The photograph is a close-up of the affected area: 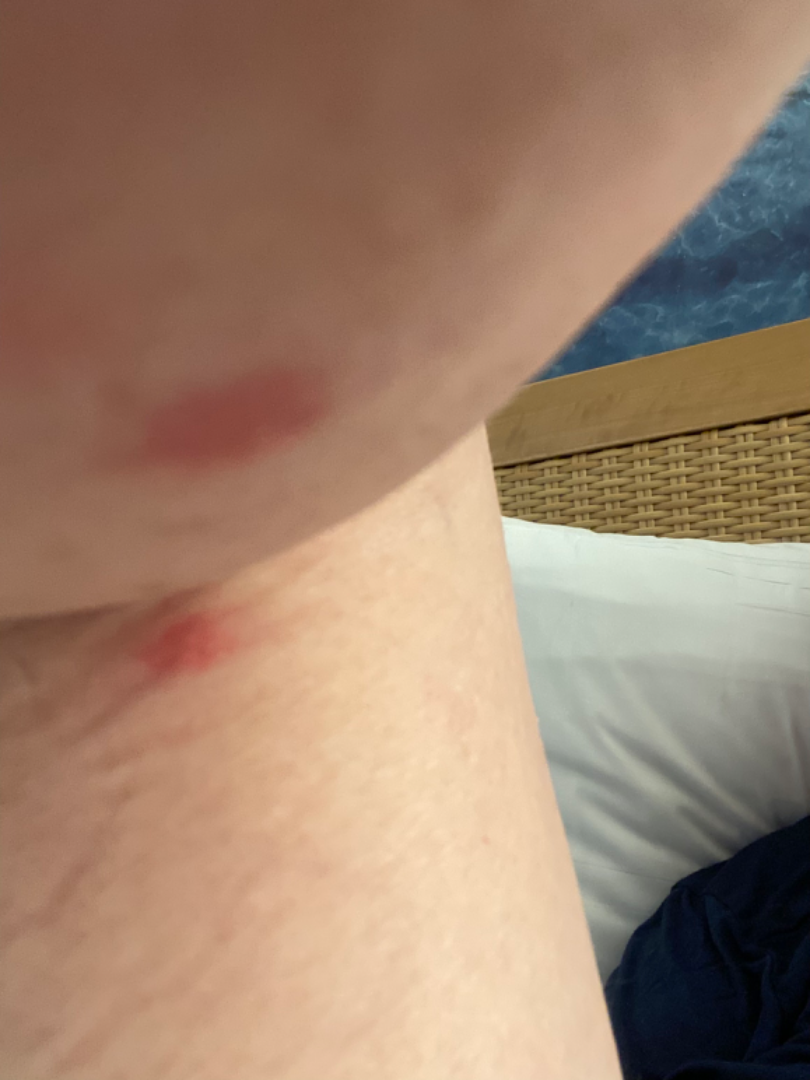{"assessment": "indeterminate", "duration": "less than one week", "symptoms": "itching", "texture": "raised or bumpy", "patient_category": "a rash"}